Present for less than one week. The photo was captured at an angle. The affected area is the arm and back of the hand:
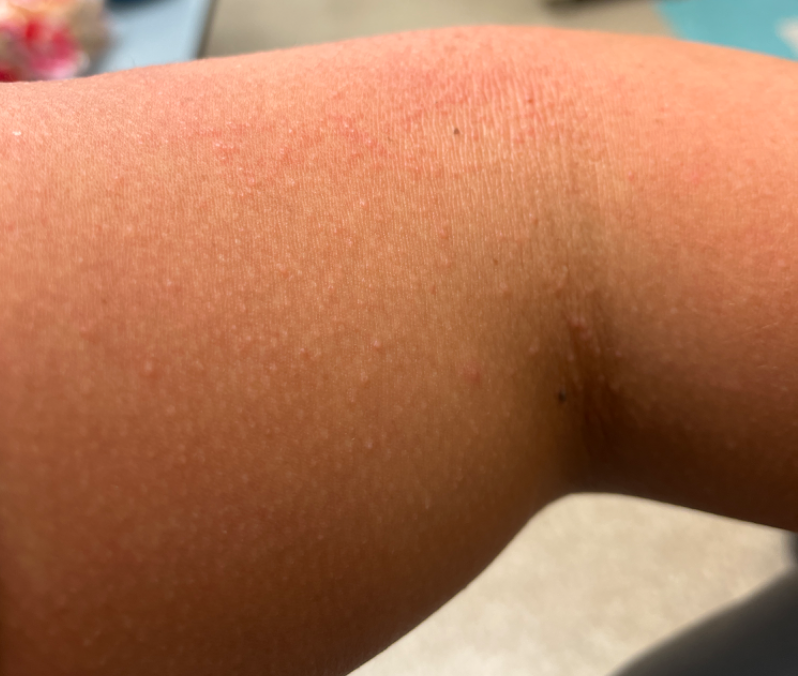Eczema and Acute and chronic dermatitis were considered with similar weight.